Female subject, age 30–39. Texture is reported as raised or bumpy and rough or flaky. The photograph was taken at a distance. Reported lesion symptoms include enlargement and itching. Present for one to four weeks.
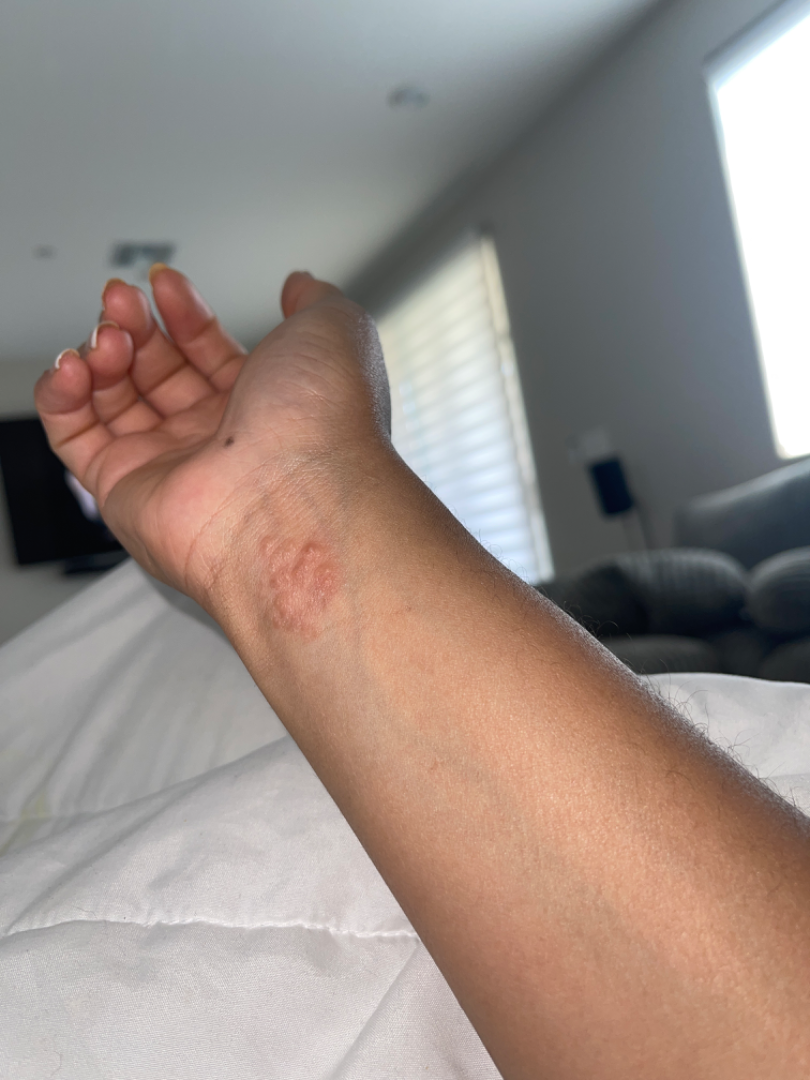A single dermatologist reviewed the case: the primary impression is Allergic Contact Dermatitis; the differential also includes Impetigo; also raised was Herpes Zoster.